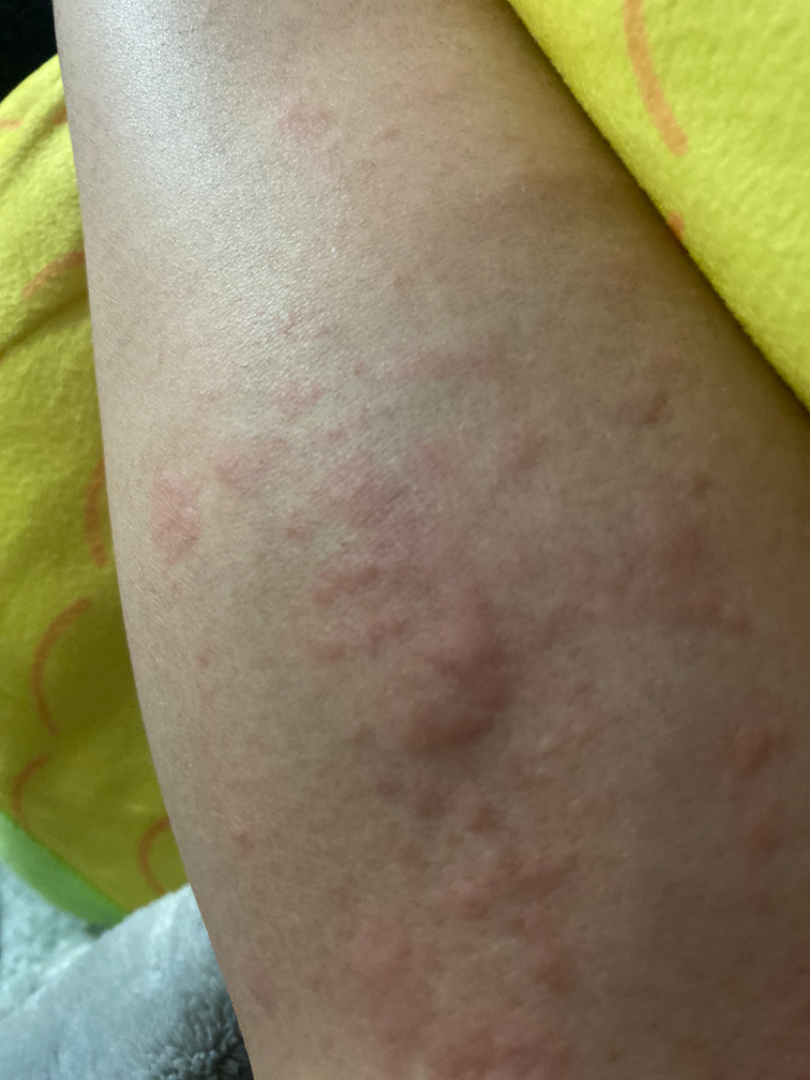Findings: The reviewing clinician's impression was: in keeping with Urticaria.